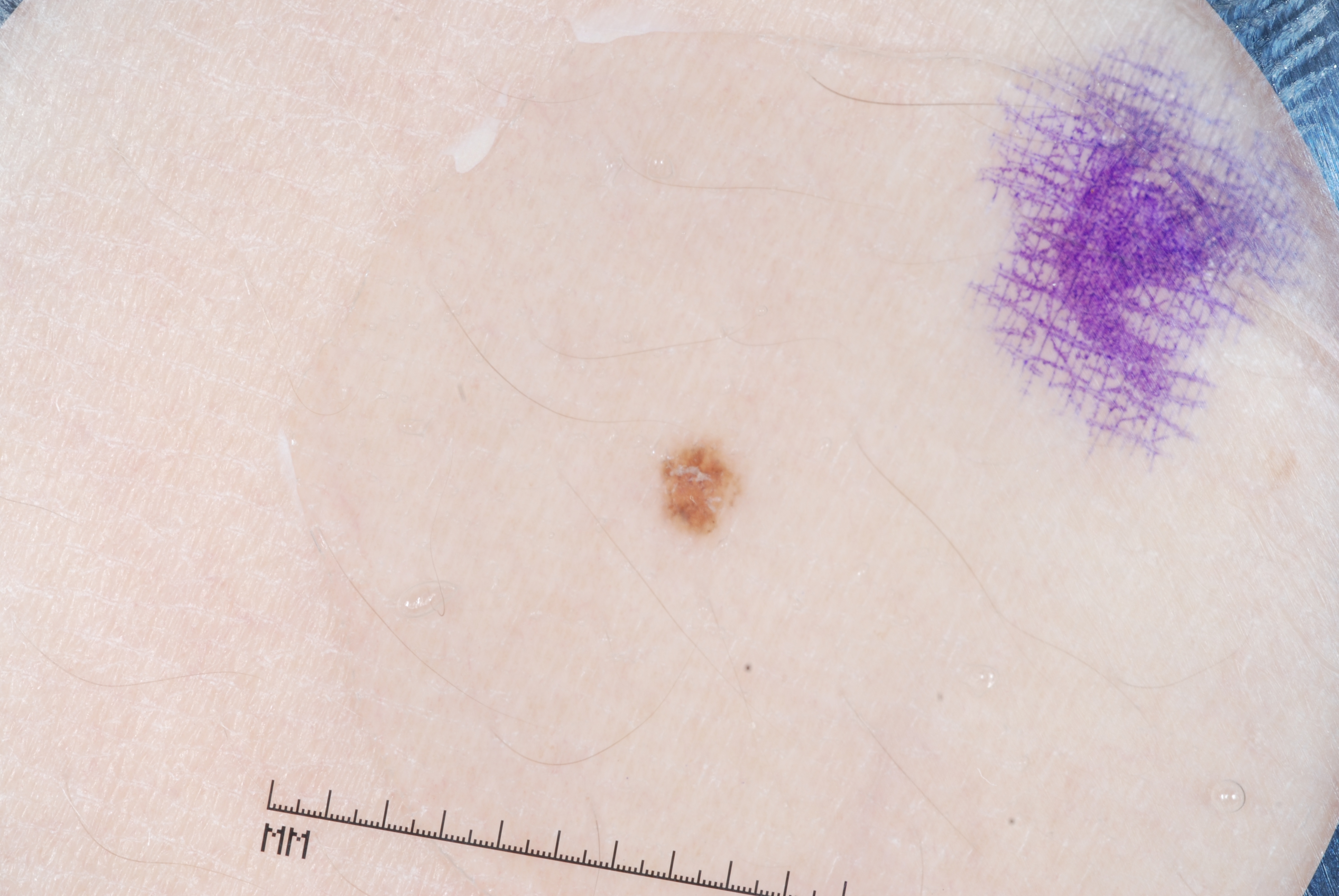A male subject aged around 25. A dermoscopic image of a skin lesion. The lesion spans <box>659, 439, 742, 538</box>. Dermoscopic review identifies no streaks, negative network, pigment network, or milia-like cysts. Clinically diagnosed as a melanocytic nevus, a benign skin lesion.